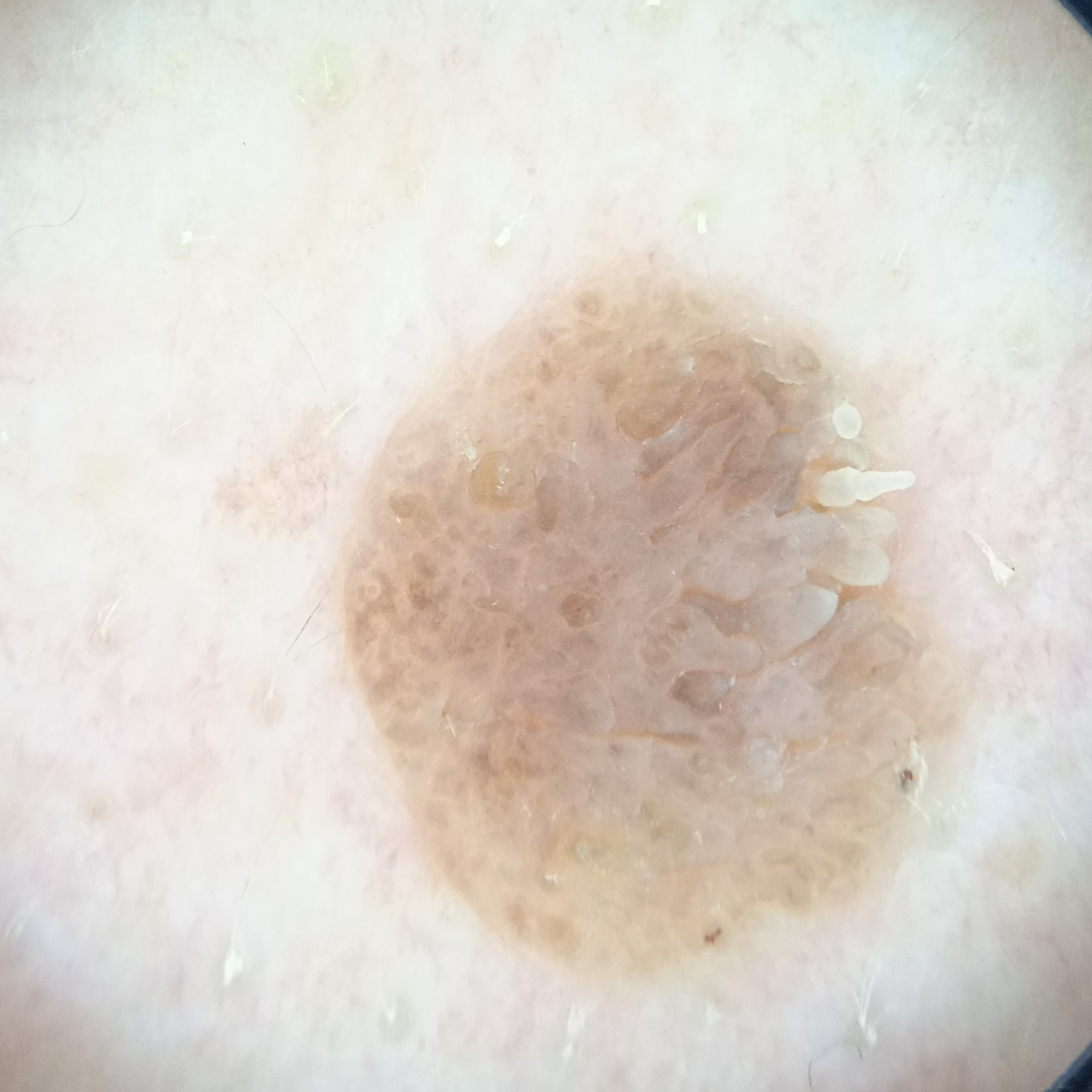<skin_lesion>
  <patient>
    <age>64</age>
    <sex>male</sex>
  </patient>
  <image>dermoscopic image</image>
  <lesion_location>the back</lesion_location>
  <lesion_size>
    <diameter_mm>8.2</diameter_mm>
  </lesion_size>
  <diagnosis>
    <name>seborrheic keratosis</name>
    <malignancy>benign</malignancy>
    <unanimous>true</unanimous>
  </diagnosis>
</skin_lesion>